The contributor reports the lesion is raised or bumpy · the condition has been present for less than one week · male patient, age 30–39 · the photograph is a close-up of the affected area · the affected area is the leg · symptoms reported: itching · the patient described the issue as a rash — 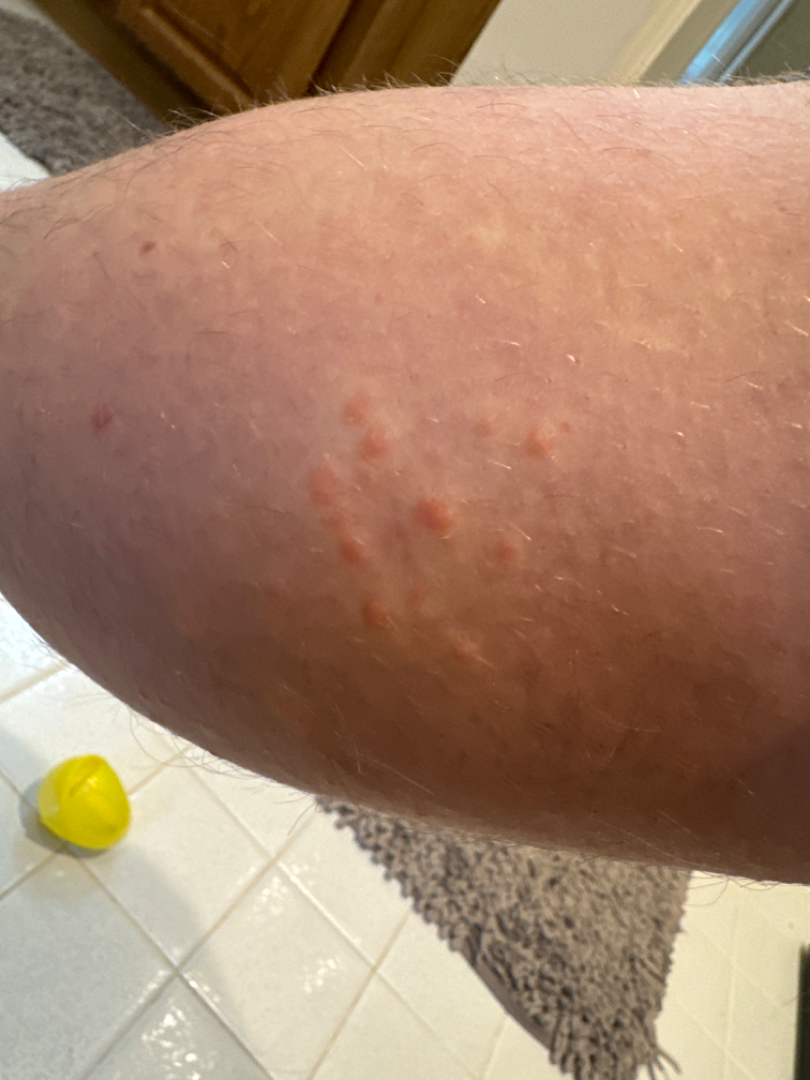  differential:
    Insect Bite: 0.67
    Hypersensitivity: 0.33